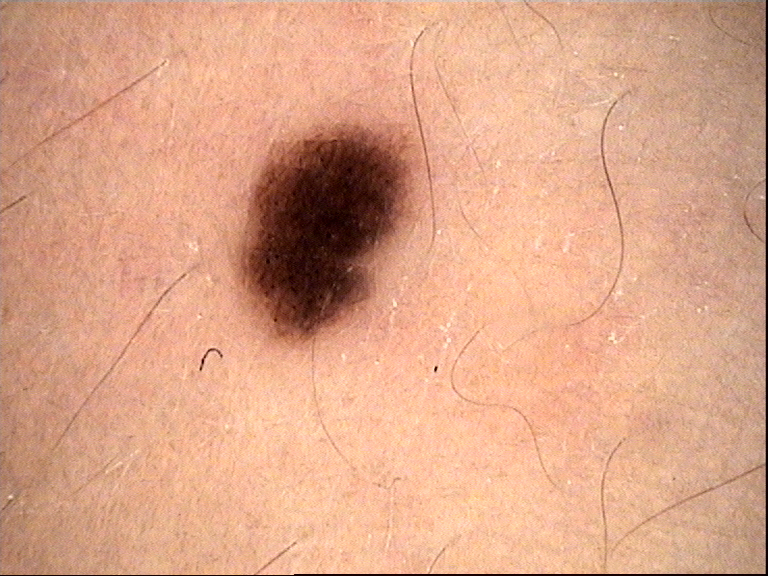Case:
* imaging · dermatoscopy
* label · dysplastic junctional nevus (expert consensus)